A clinical close-up of a skin lesion; a female patient 73 years of age:
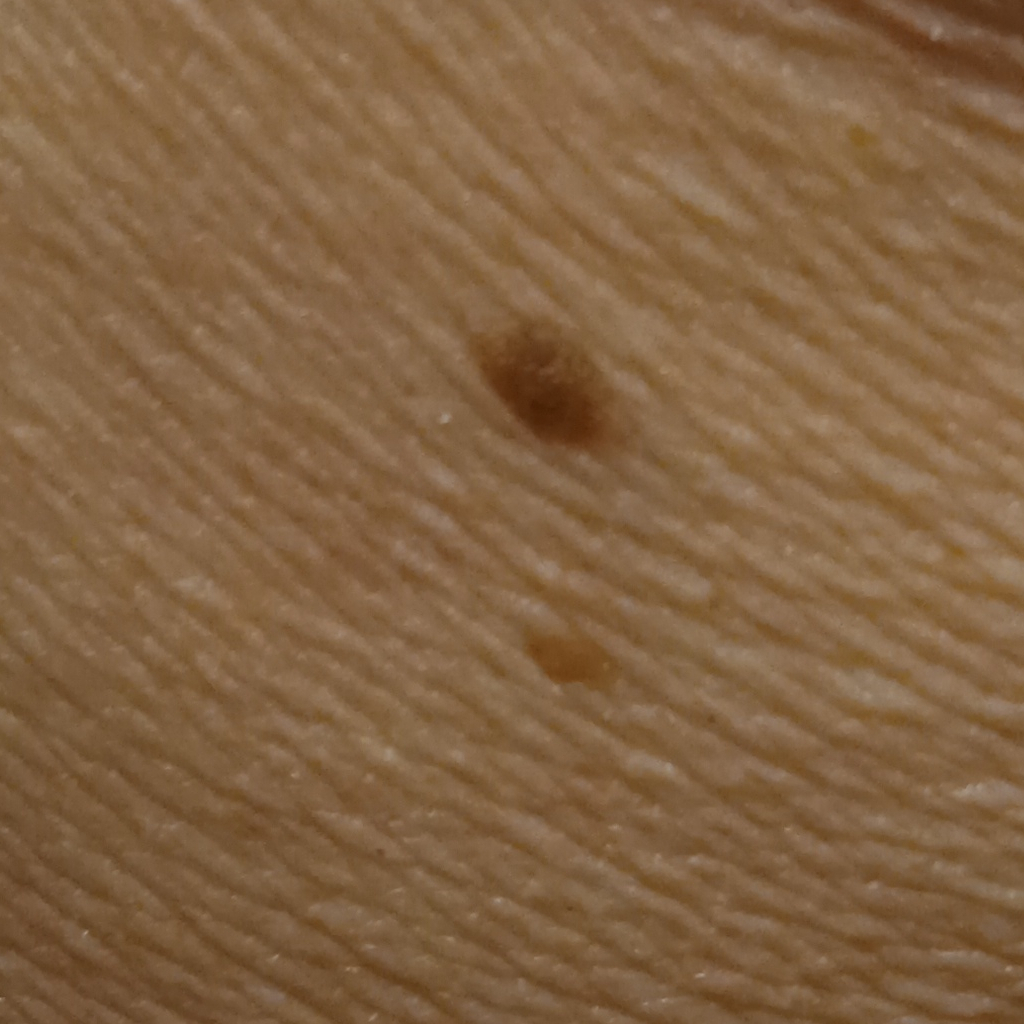The lesion is on the back. Measuring roughly 6 mm. The diagnostic impression was a seborrheic keratosis.